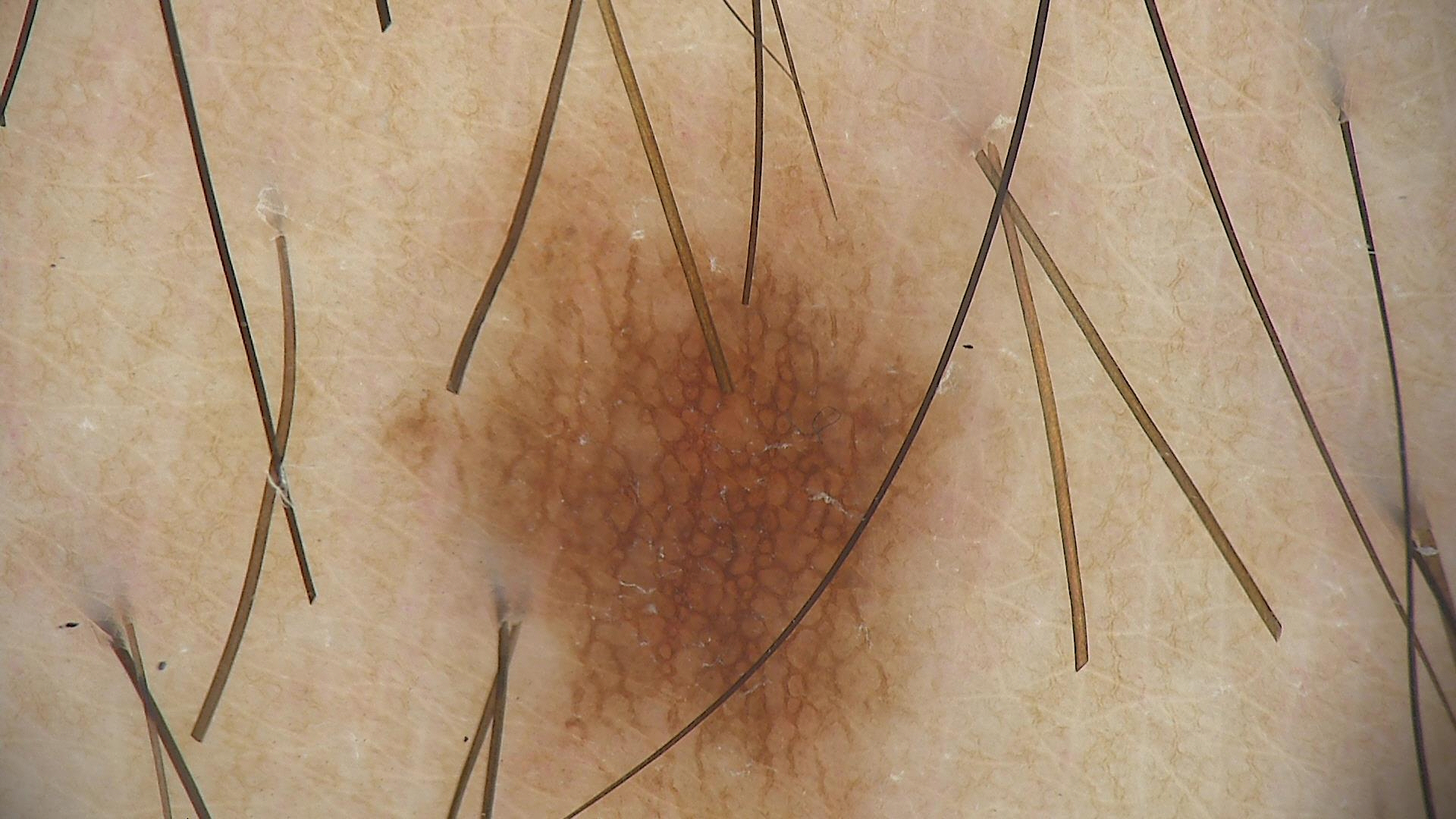A dermoscopic close-up of a skin lesion. The diagnosis was a dysplastic junctional nevus.